A close-up photograph · the lesion involves the arm · the contributor is a female aged 30–39: 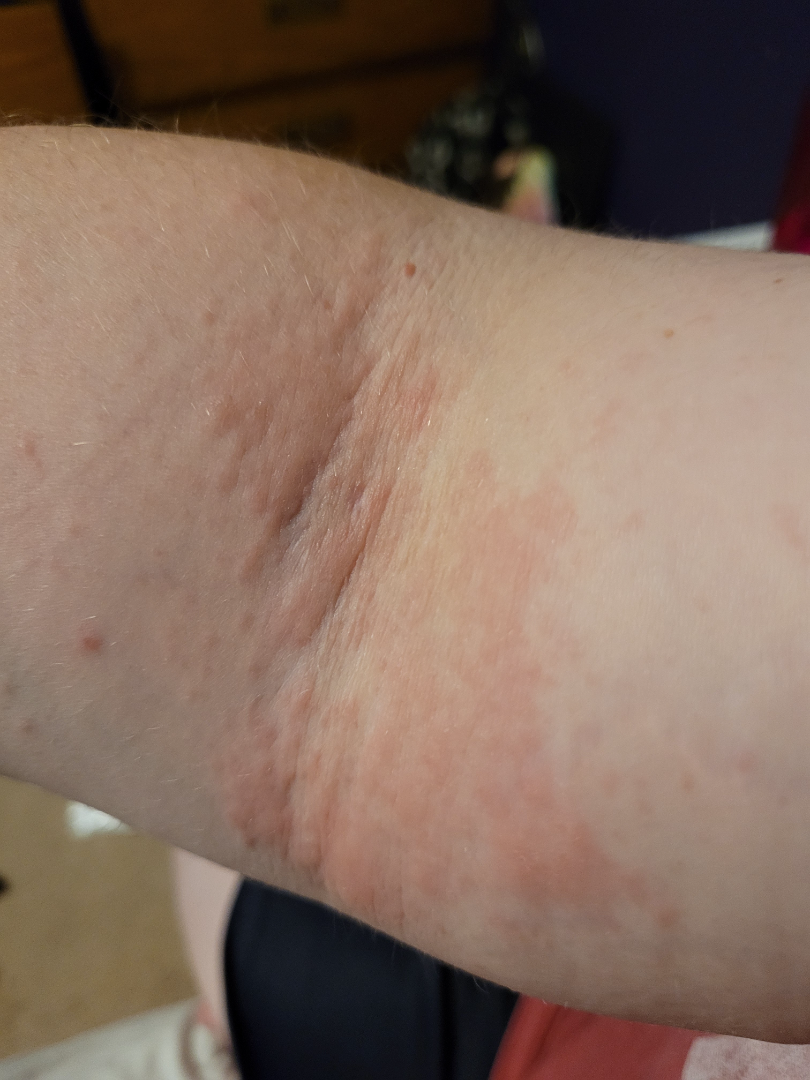Clinical context: Symptoms reported: enlargement, bothersome appearance and itching. Self-categorized by the patient as a rash. The lesion is described as raised or bumpy. Assessment: A single dermatologist reviewed the case: the impression is Eczema.